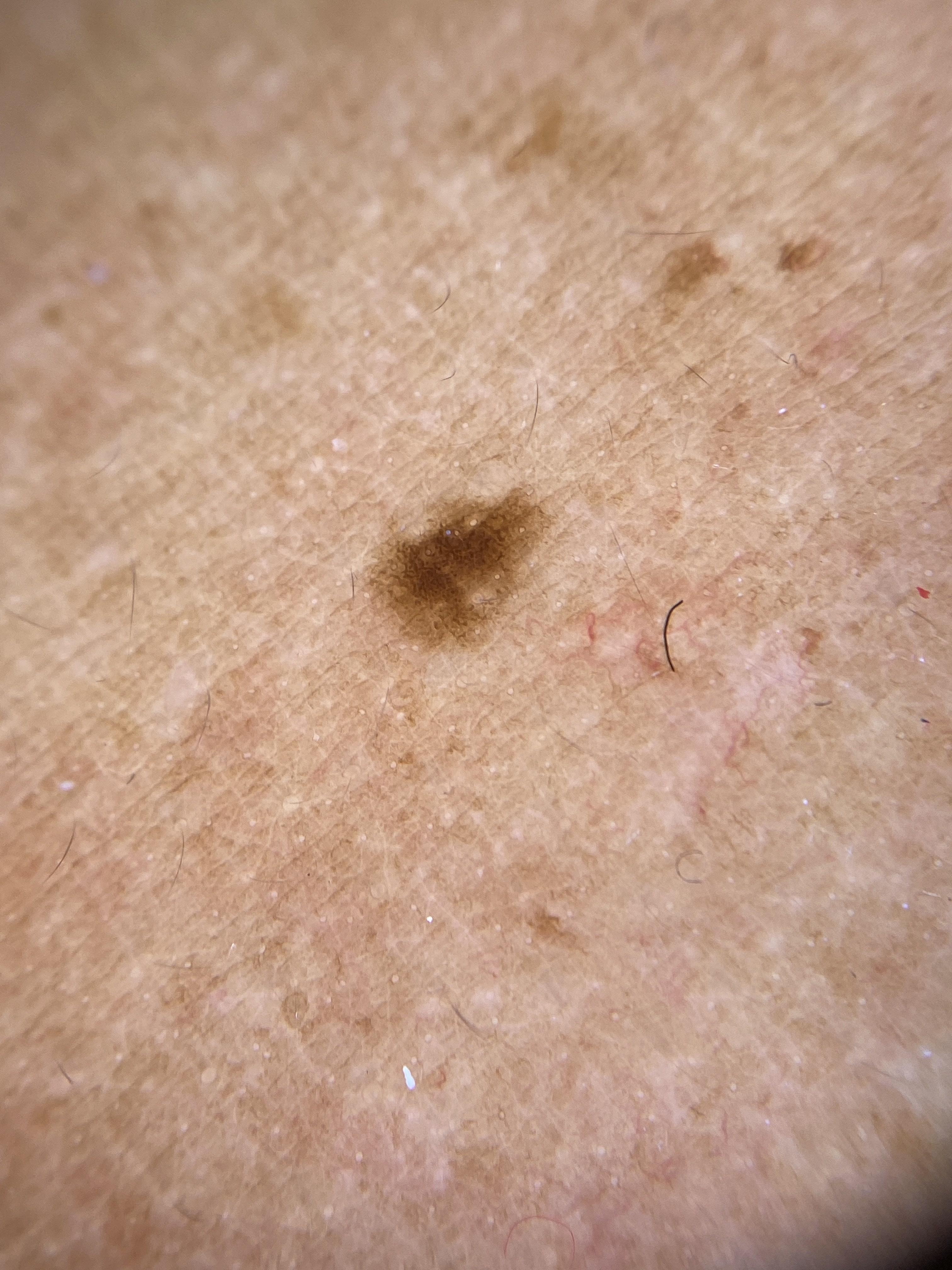image = contact-polarized dermoscopy; skin phototype = II; patient = female, aged 33 to 37; body site = the trunk; diagnostic label = Nevus (clinical impression).